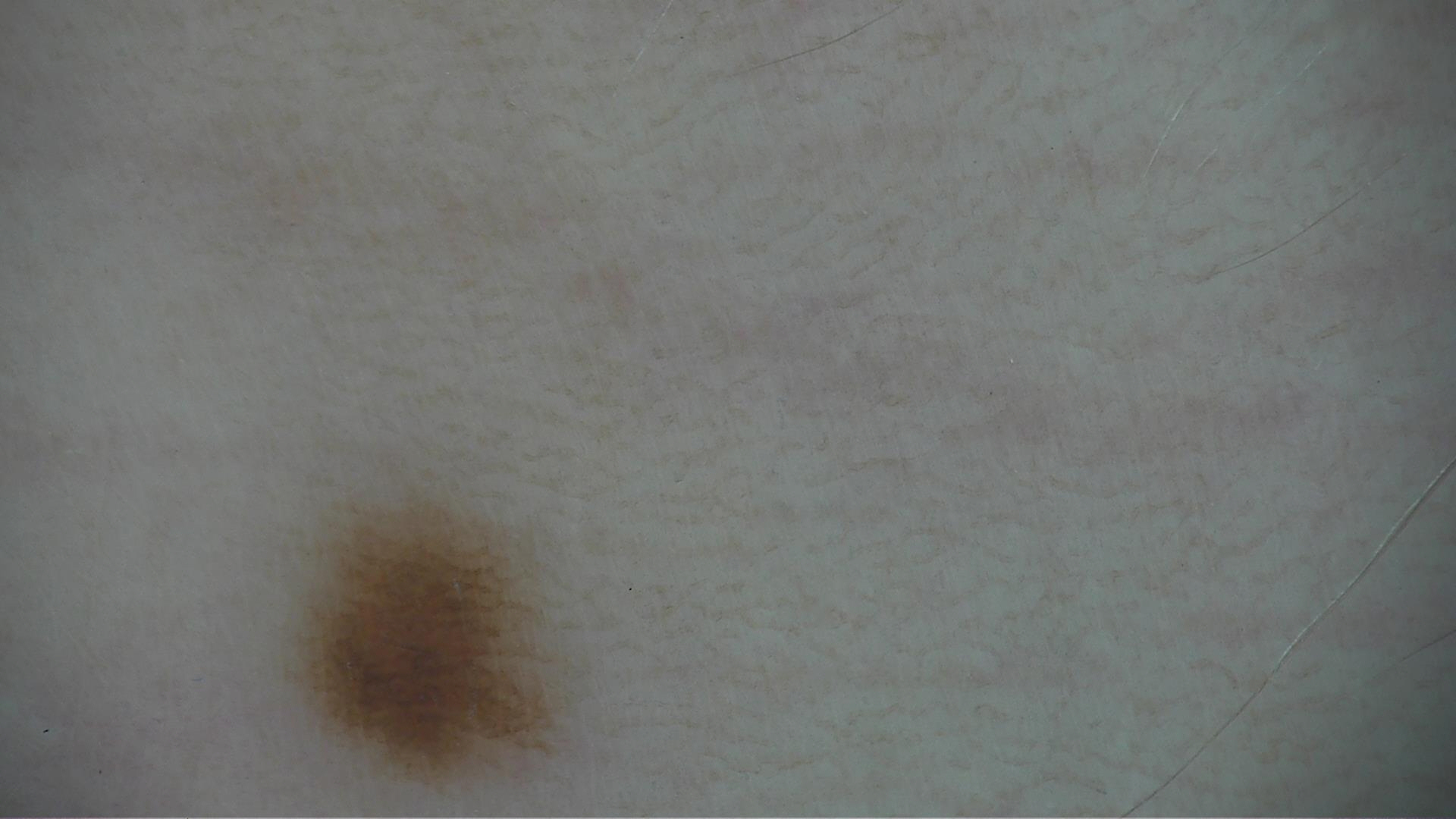Dermoscopy of a skin lesion. This is a banal lesion. Diagnosed as a junctional nevus.